The photograph was taken at an angle. The contributor is male. Located on the leg.
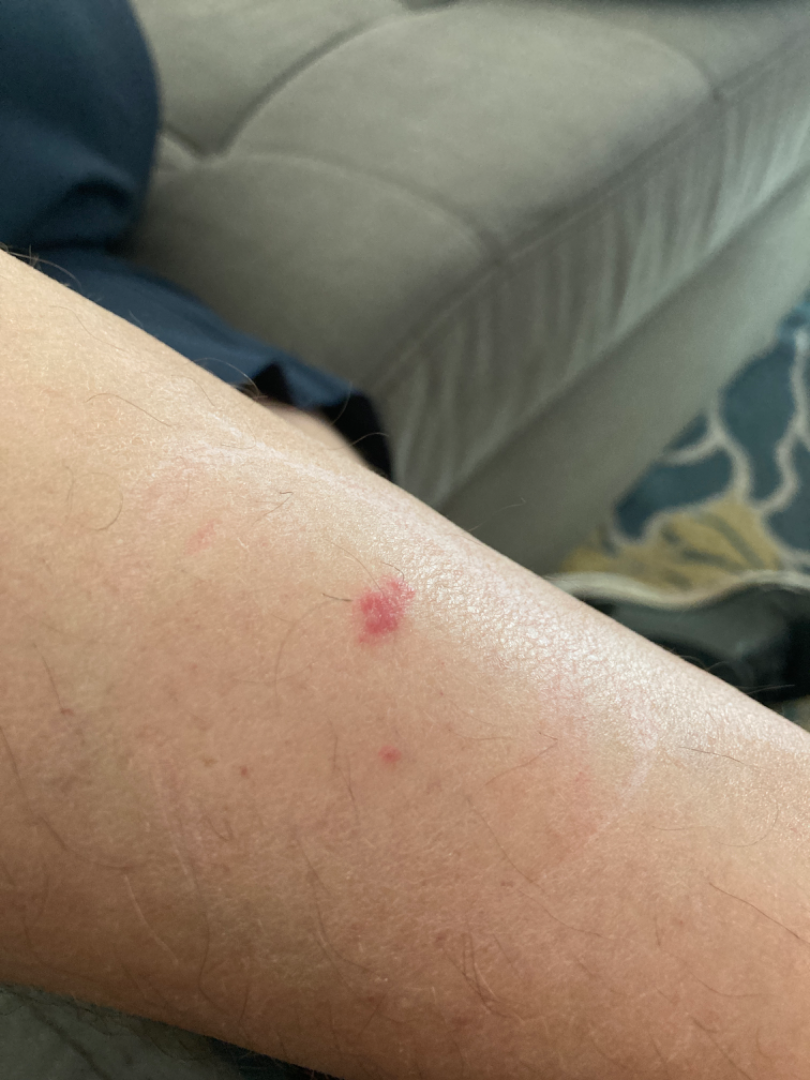On dermatologist assessment of the image: the differential, in no particular order, includes Eczema, Allergic Contact Dermatitis and Basal Cell Carcinoma.